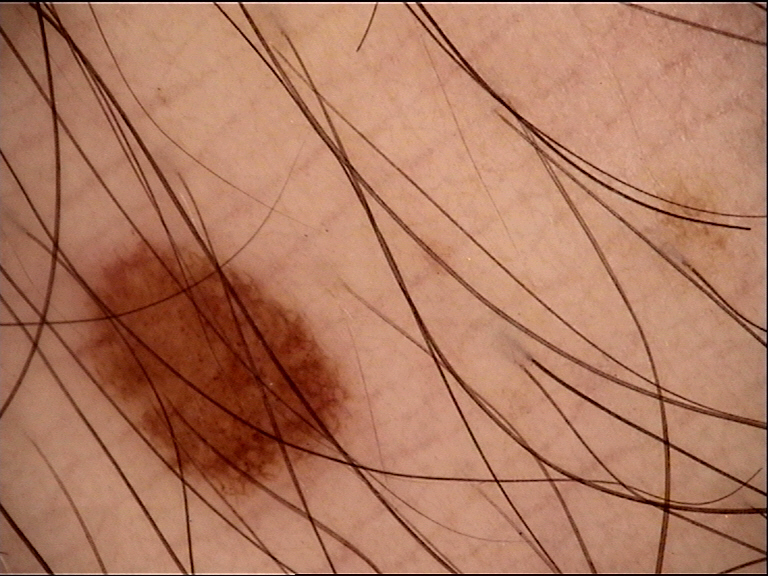Summary:
A dermoscopic photograph of a skin lesion.
Impression:
Labeled as a benign lesion — a dysplastic junctional nevus.